A dermoscopic close-up of a skin lesion.
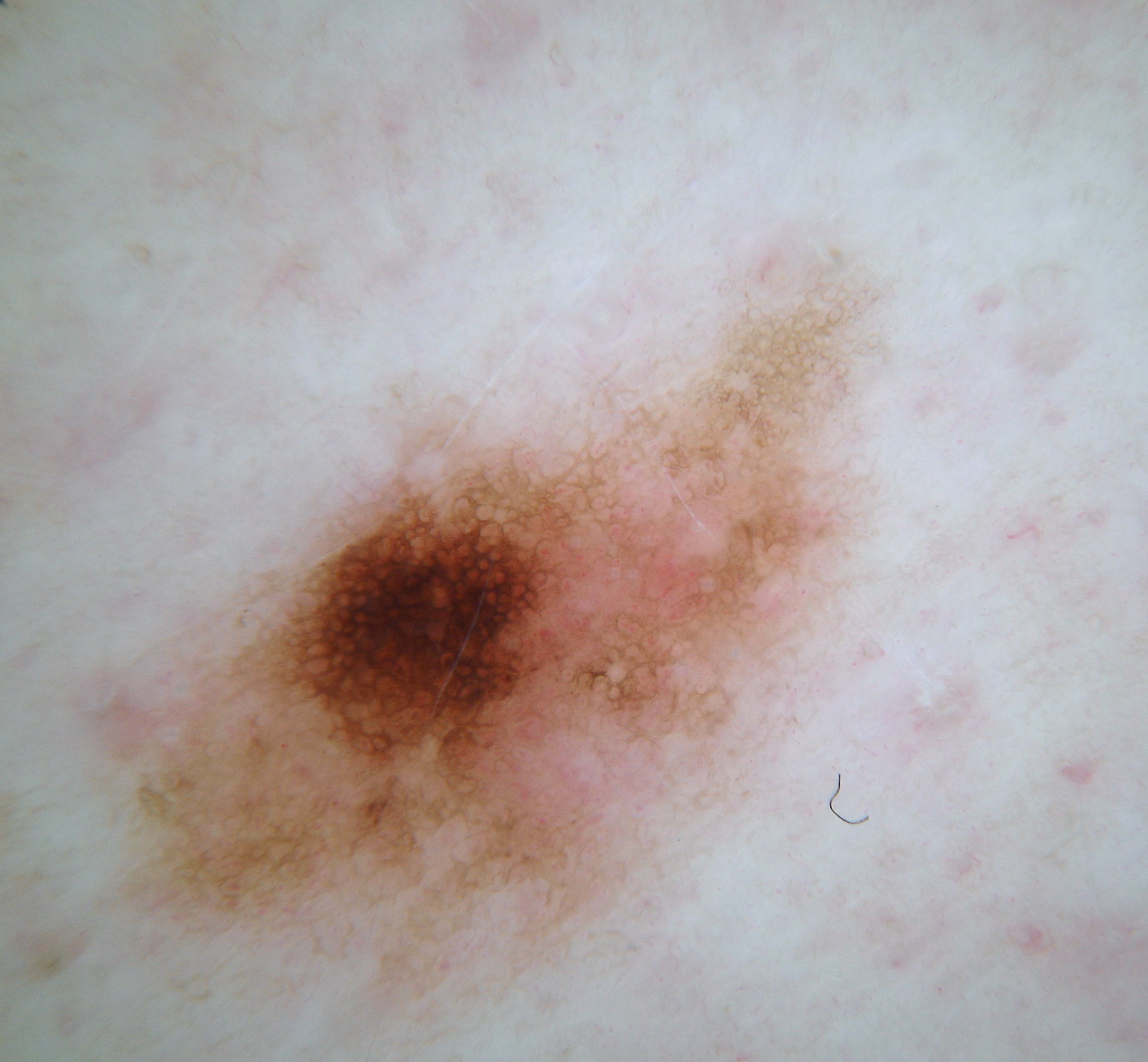As (left, top, right, bottom), the lesion occupies the region [75,224,911,1037].
The lesion was assessed as a melanocytic nevus.